A dermatoscopic image of a skin lesion.
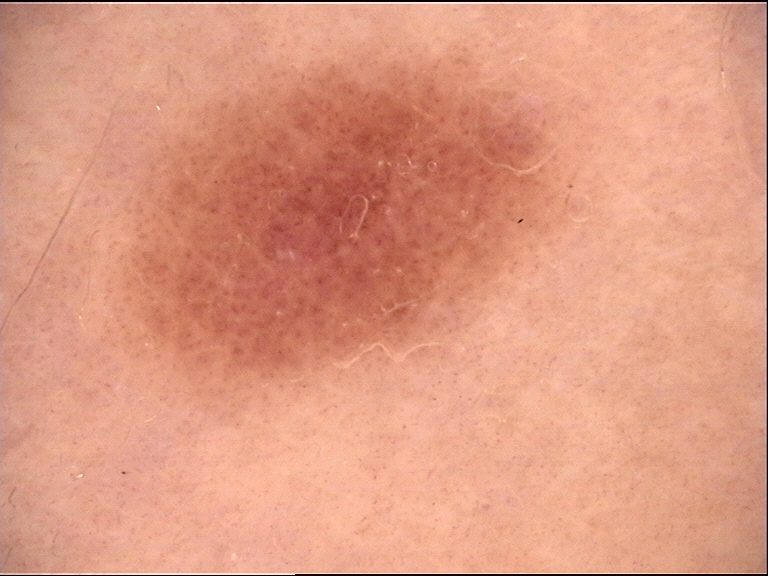Impression: Diagnosed as a benign lesion — a dysplastic junctional nevus.